This image was taken at an angle; the patient is 40–49, female; located on the arm: 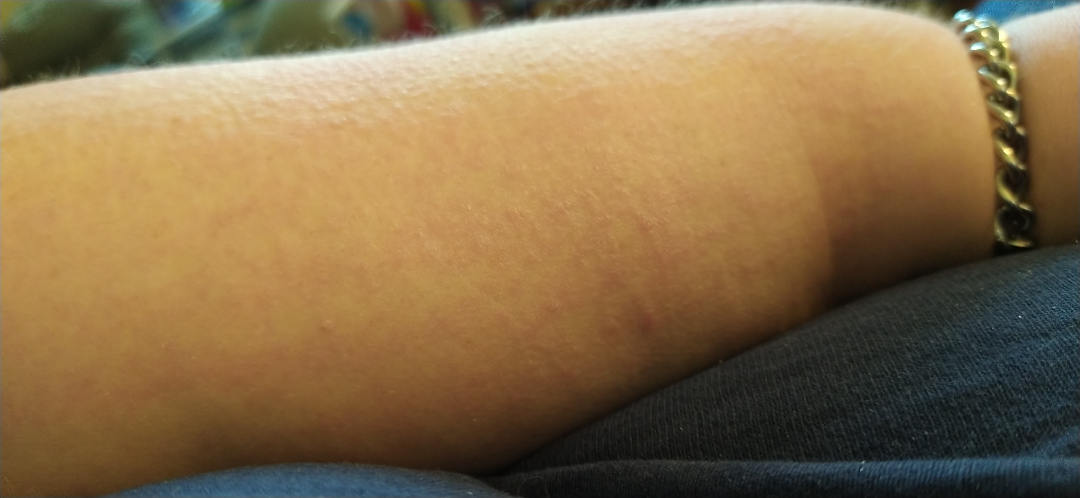Associated systemic symptoms include mouth sores, fatigue and joint pain. Symptoms reported: darkening and itching. The patient notes the lesion is raised or bumpy. Reported duration is more than one year. The patient considered this a rash. On remote dermatologist review, the leading consideration is Eczema; also consider Acute dermatitis, NOS; less likely is Allergic Contact Dermatitis; lower on the differential is Viral Exanthem; less probable is Keratosis pilaris.